Collected as part of a research study, without a referral diagnosis; a dermoscopy image of a skin lesion: 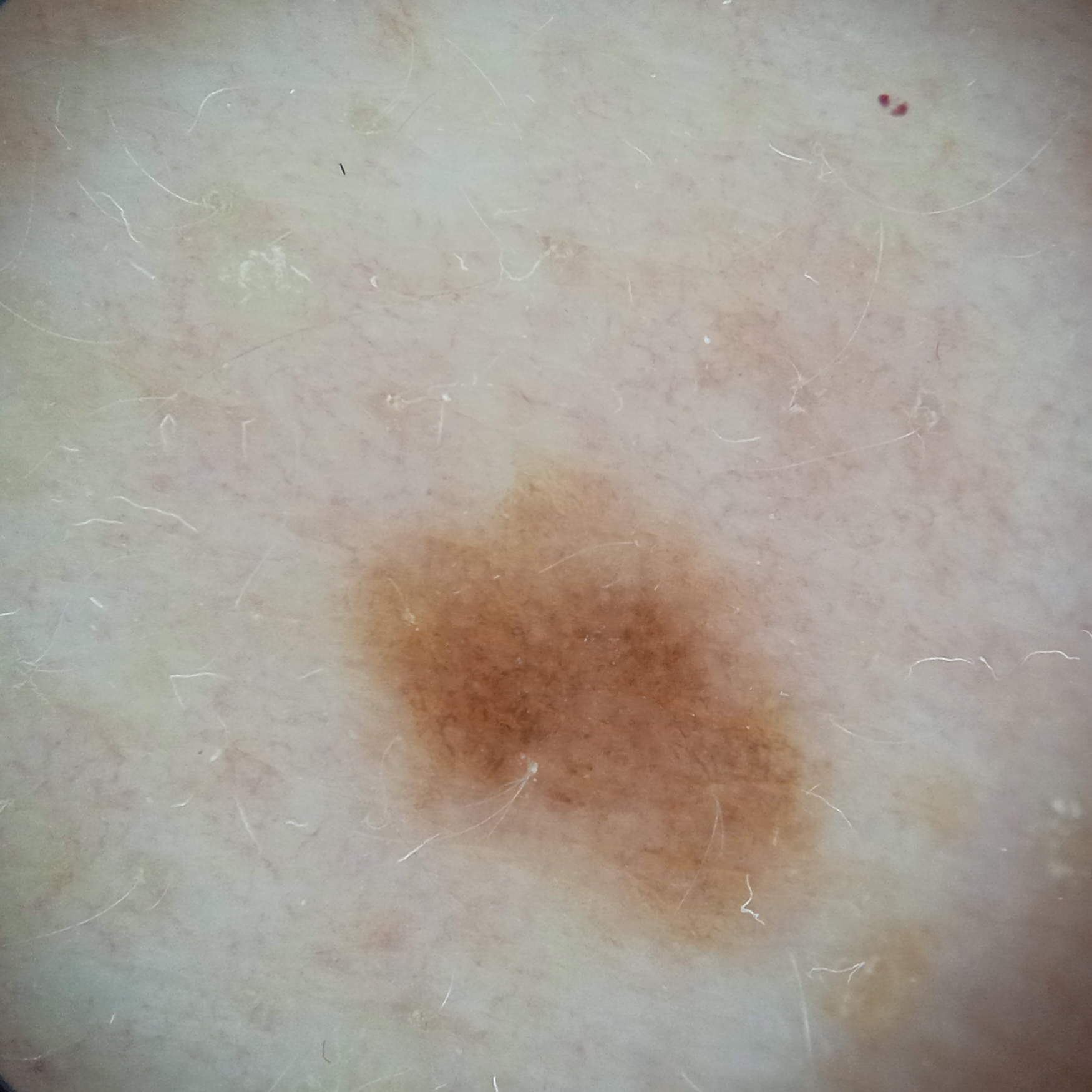| field | value |
|---|---|
| anatomic site | the back |
| lesion size | 6.3 mm |
| diagnostic label | melanocytic nevus (dermatologist consensus) |